A skin lesion imaged with a dermatoscope:
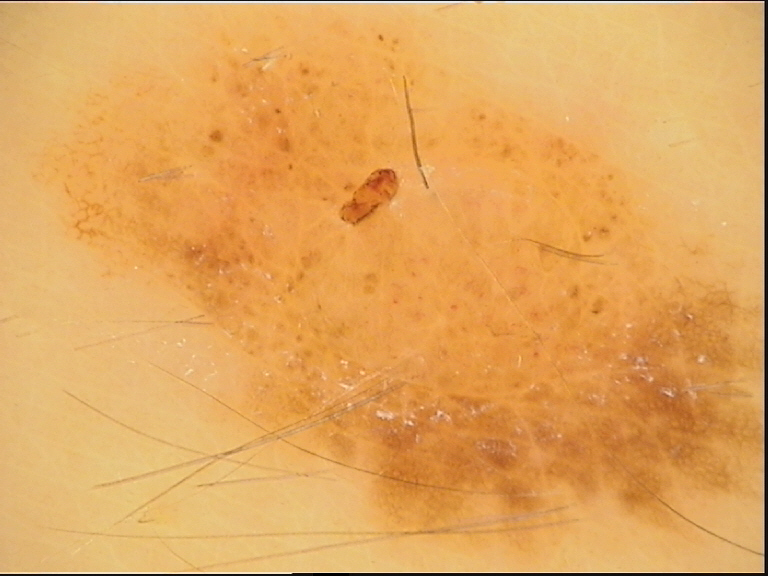Q: What was the diagnostic impression?
A: dysplastic compound nevus (expert consensus)